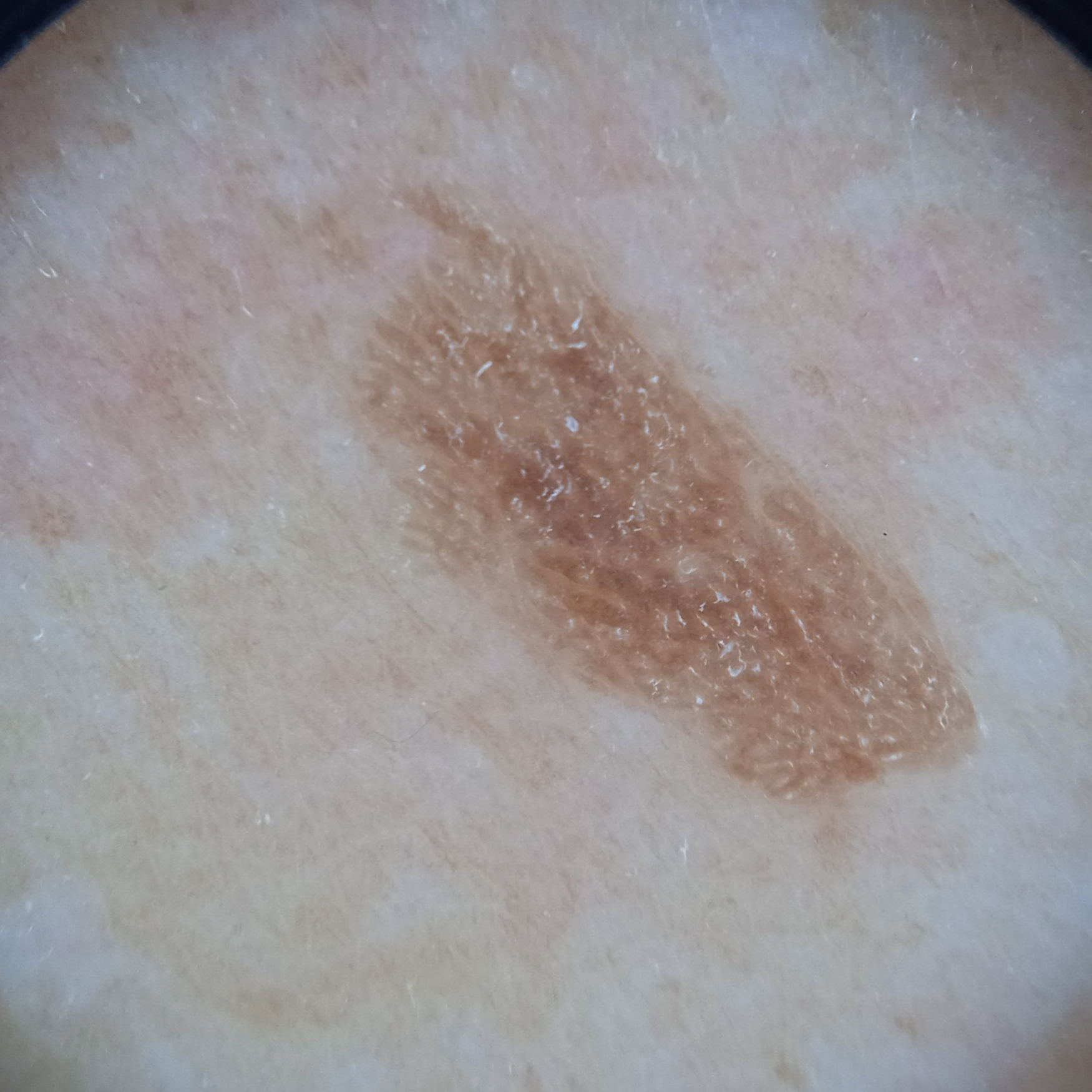The patient describes having a moderate number of moles. A dermoscopic image of a skin lesion. Acquired for a research image collection, with no referral diagnosis. By self-report, a personal history of cancer, a personal history of skin cancer, no sunbed use, and no prior organ transplant. The patient says their skin tans without first burning. The lesion is on the back. The lesion is about 8.4 mm across. The diagnostic impression was a seborrheic keratosis.